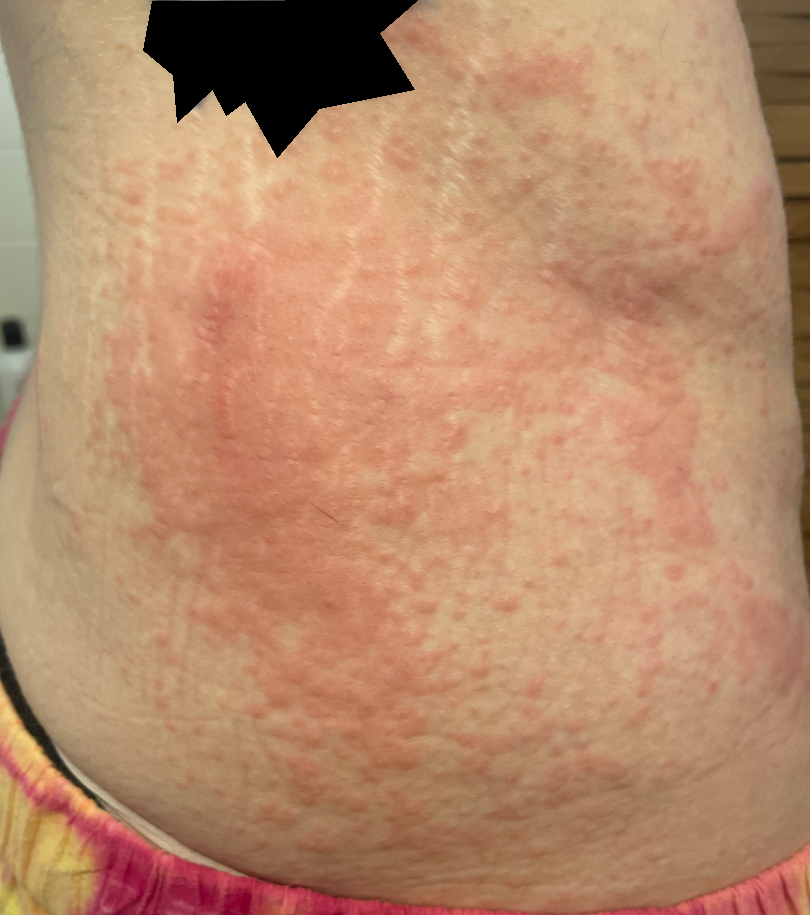Close-up view. The lesion involves the leg, arm and back of the torso. Urticaria (possible); Drug Rash (possible); Leukocytoclastic Vasculitis (unlikely).